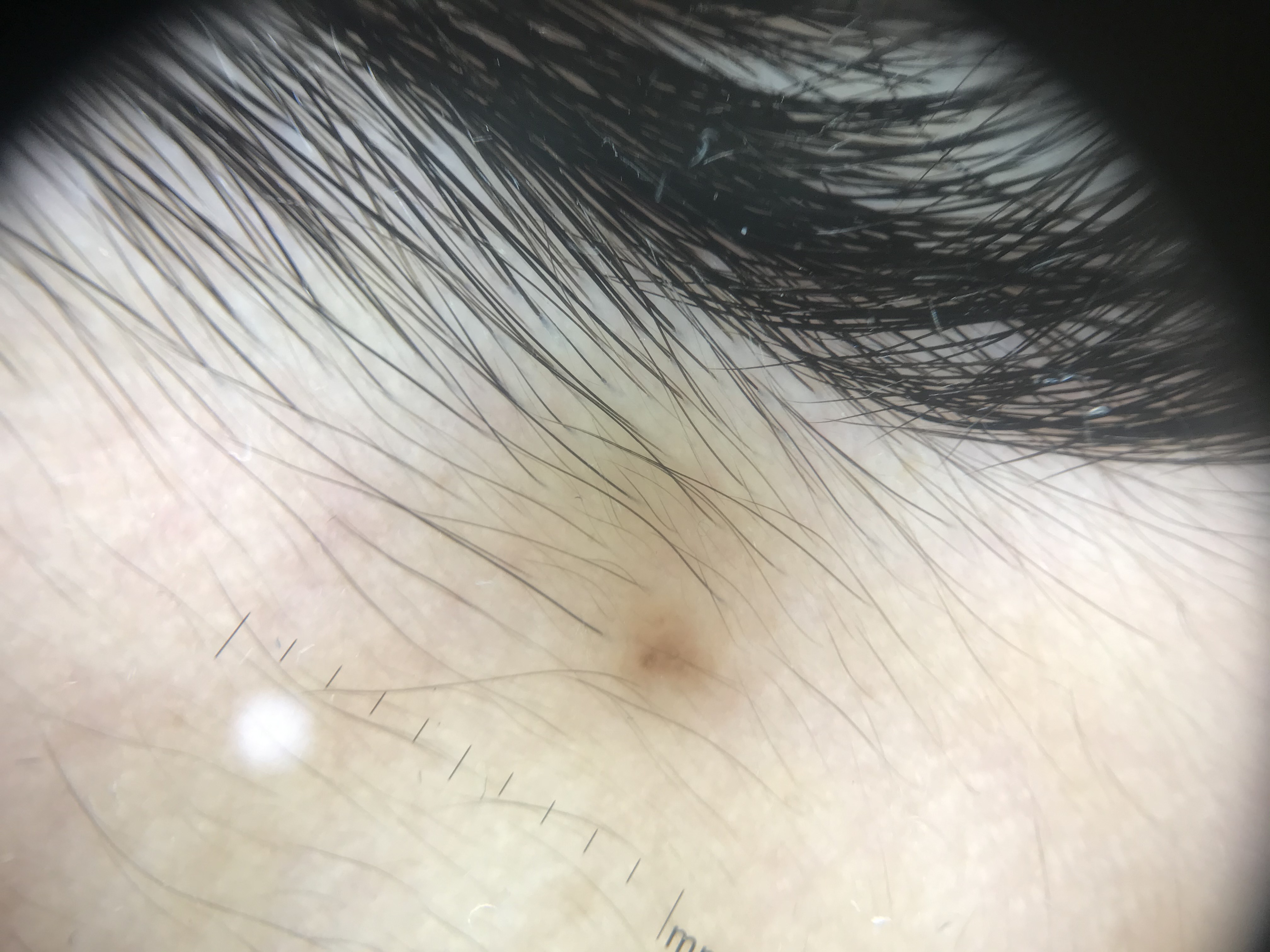Case:
A dermoscopic close-up of a skin lesion.
Conclusion:
Consistent with a Miescher nevus.